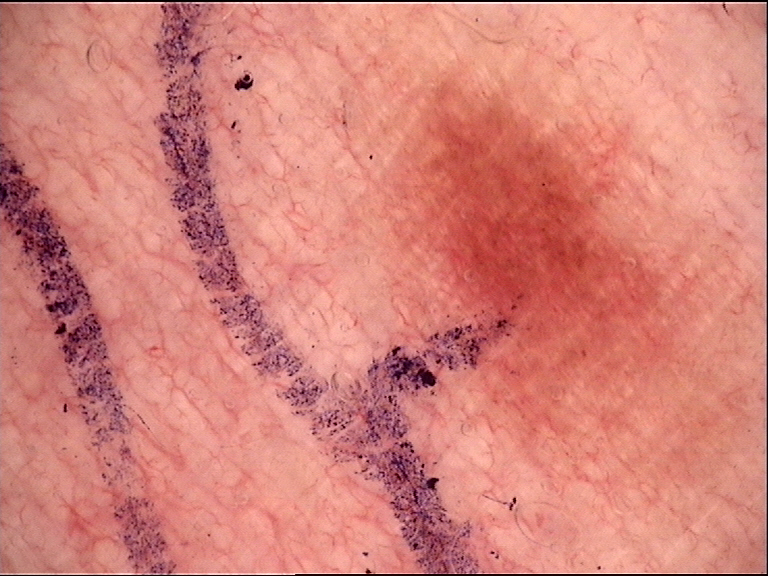- assessment — dysplastic junctional nevus (expert consensus)